Located on the top or side of the foot; the photograph is a close-up of the affected area — 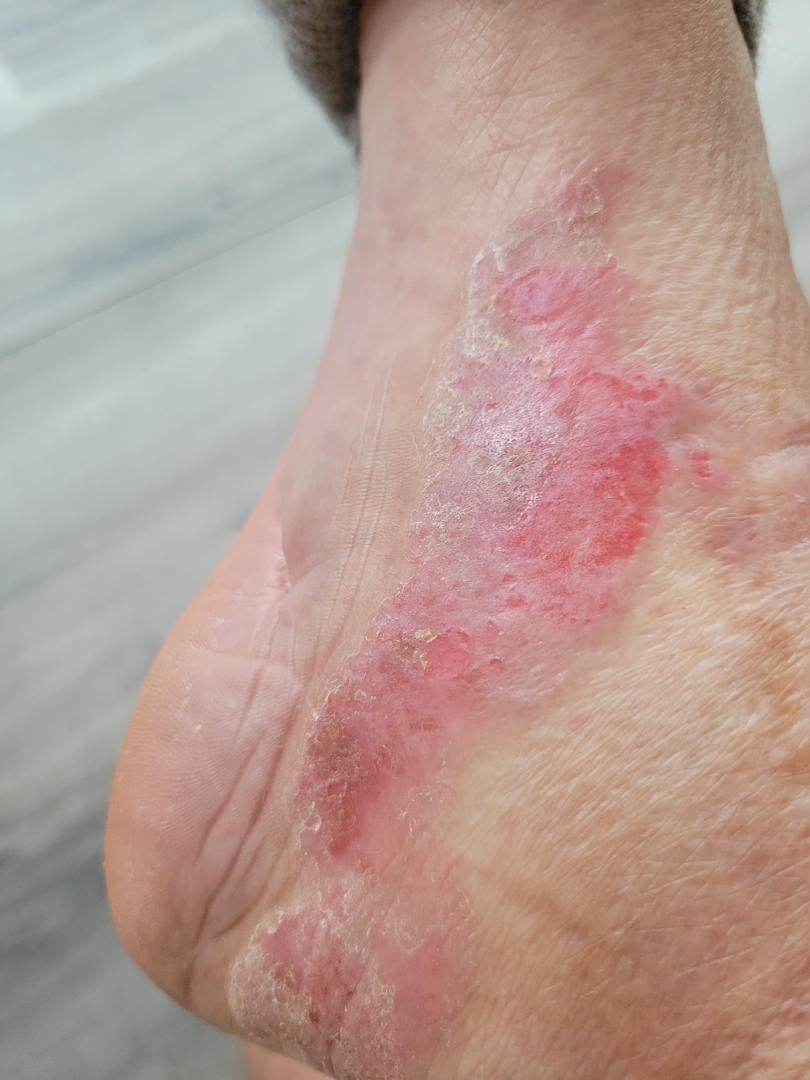On teledermatology review, the primary impression is Cutaneous T Cell Lymphoma; possibly Tinea; also on the differential is Irritant Contact Dermatitis.